A dermatoscopic image of a skin lesion.
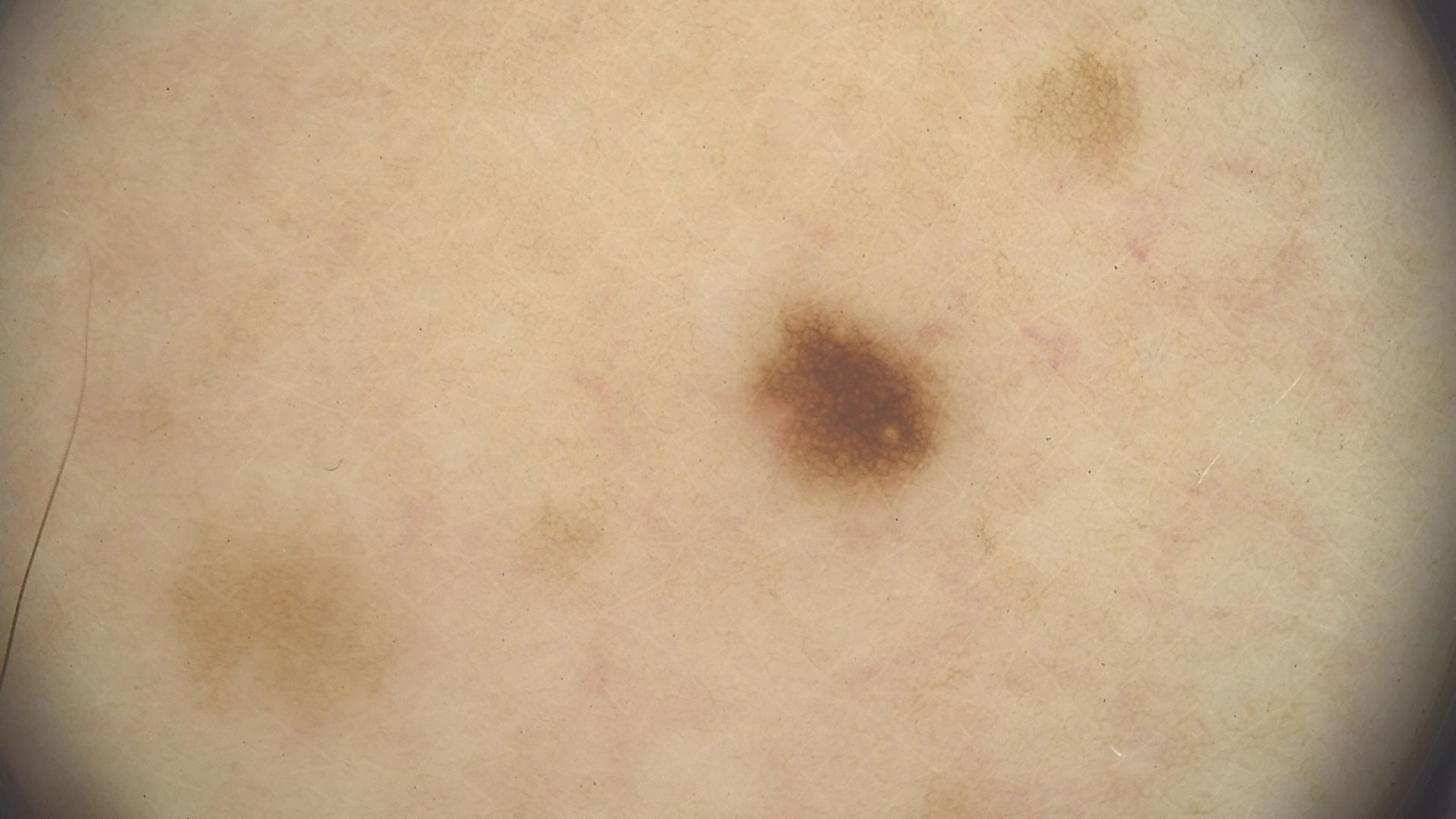This is a banal lesion. Diagnosed as a junctional nevus.